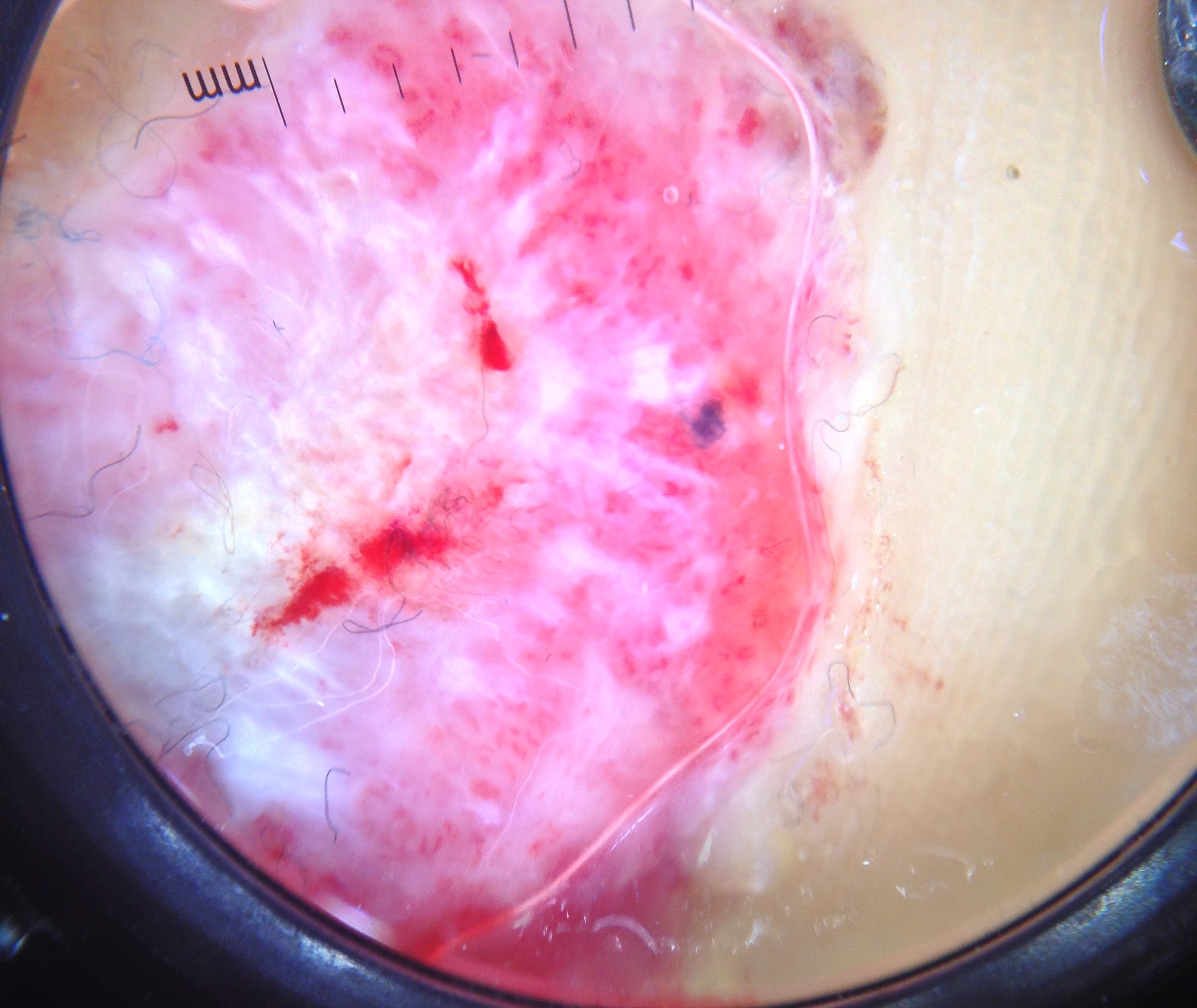Confirmed on histopathology as an acral nodular melanoma.